This is a close-up image. The contributor reports the condition has been present for less than one week. Self-categorized by the patient as skin that appeared healthy to them. Symptoms reported: itching and bothersome appearance. No constitutional symptoms were reported. Male patient, age 30–39. The lesion involves the arm:
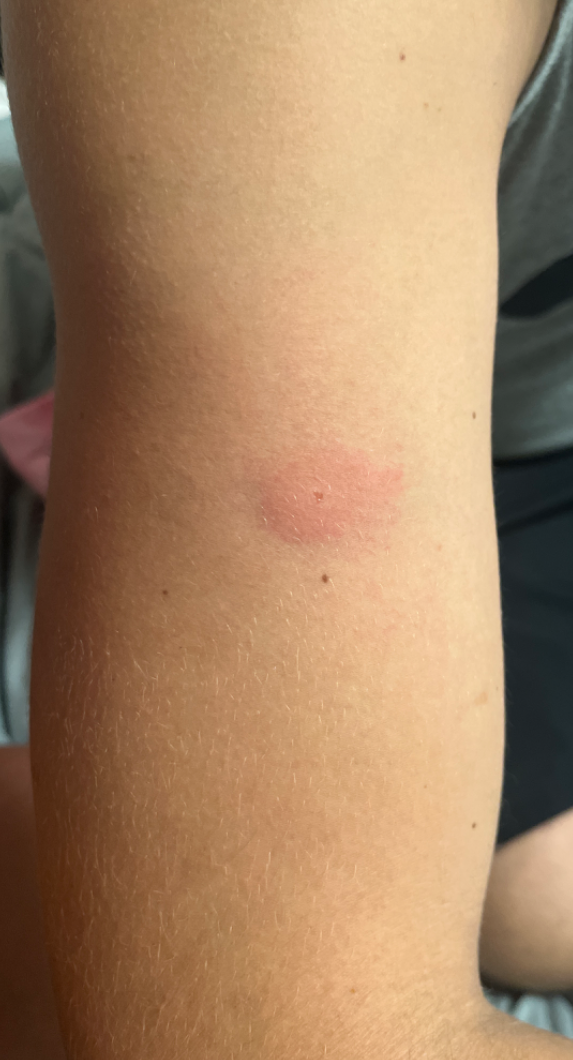The dermatologist could not determine a likely condition from the photograph alone.